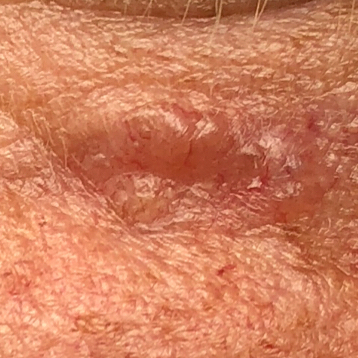By history, prior skin cancer (patient or family), pesticide exposure, alcohol use, and prior malignancy (patient or family). A clinical close-up photograph of a skin lesion. The patient is FST III. A male patient aged 48. The lesion was found on the face. Measuring about 7 × 5 mm. Confirmed on histopathology as a malignant skin lesion — a basal cell carcinoma.